Dermoscopy of a skin lesion:
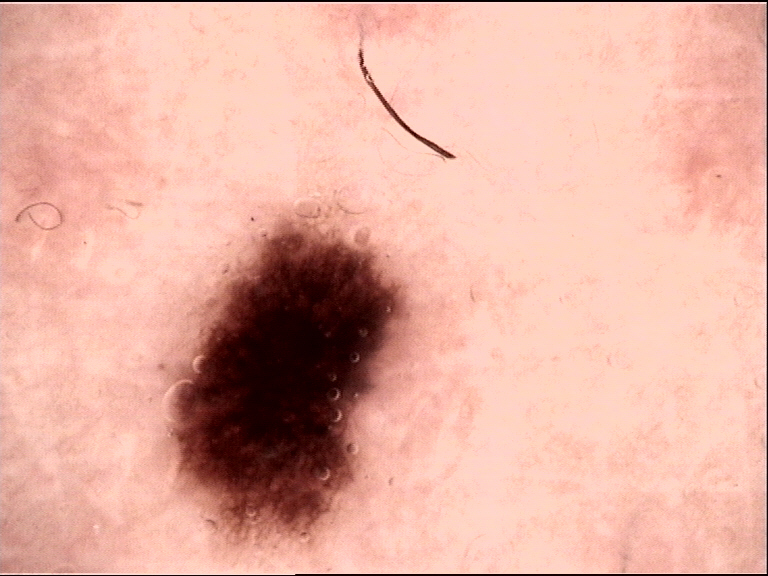| field | value |
|---|---|
| subtype | banal |
| label | junctional nevus (expert consensus) |